A dermoscopic image of a skin lesion; a female subject 26 years old; collected as part of a research study, without a referral diagnosis; numerous moles by the patient's own estimate; the patient reports a history of sunbed use, no prior organ transplant, and no personal history of cancer:
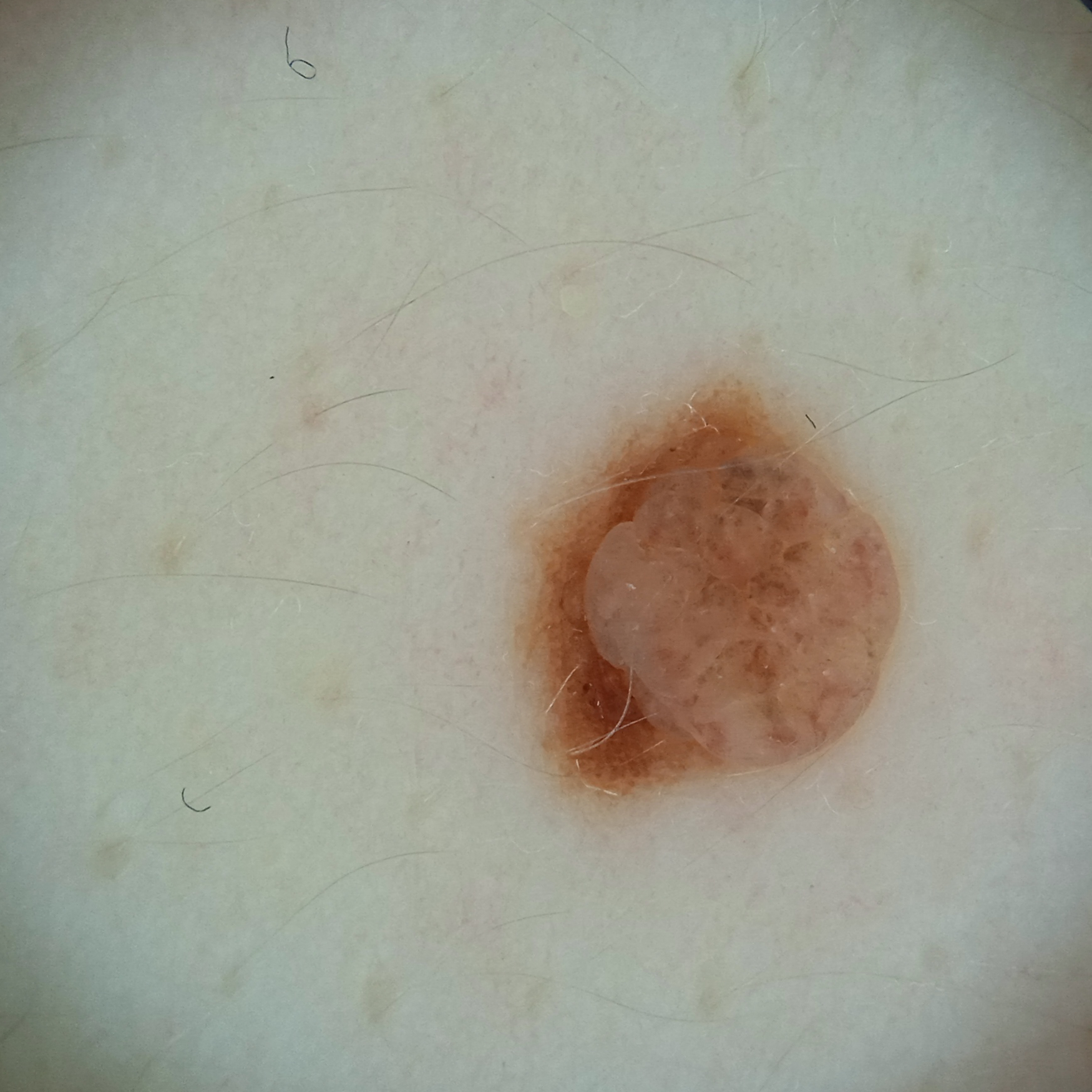Findings:
* body site: the back
* diameter: 4.5 mm
* diagnostic label: melanocytic nevus (dermatologist consensus)